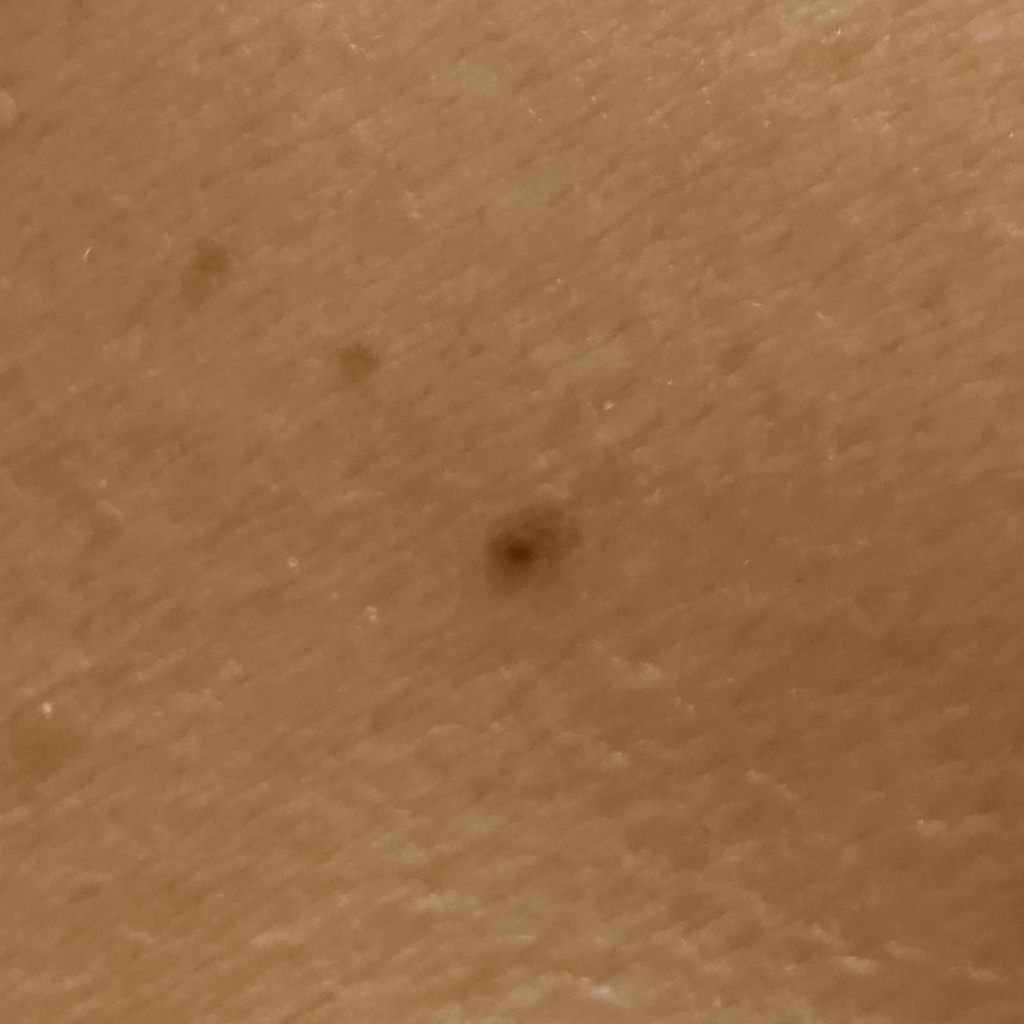Acquired for a research image collection, with no referral diagnosis. A female subject 81 years of age. Located on the back. The lesion measures approximately 2.7 mm. The consensus diagnosis for this lesion was a melanocytic nevus.